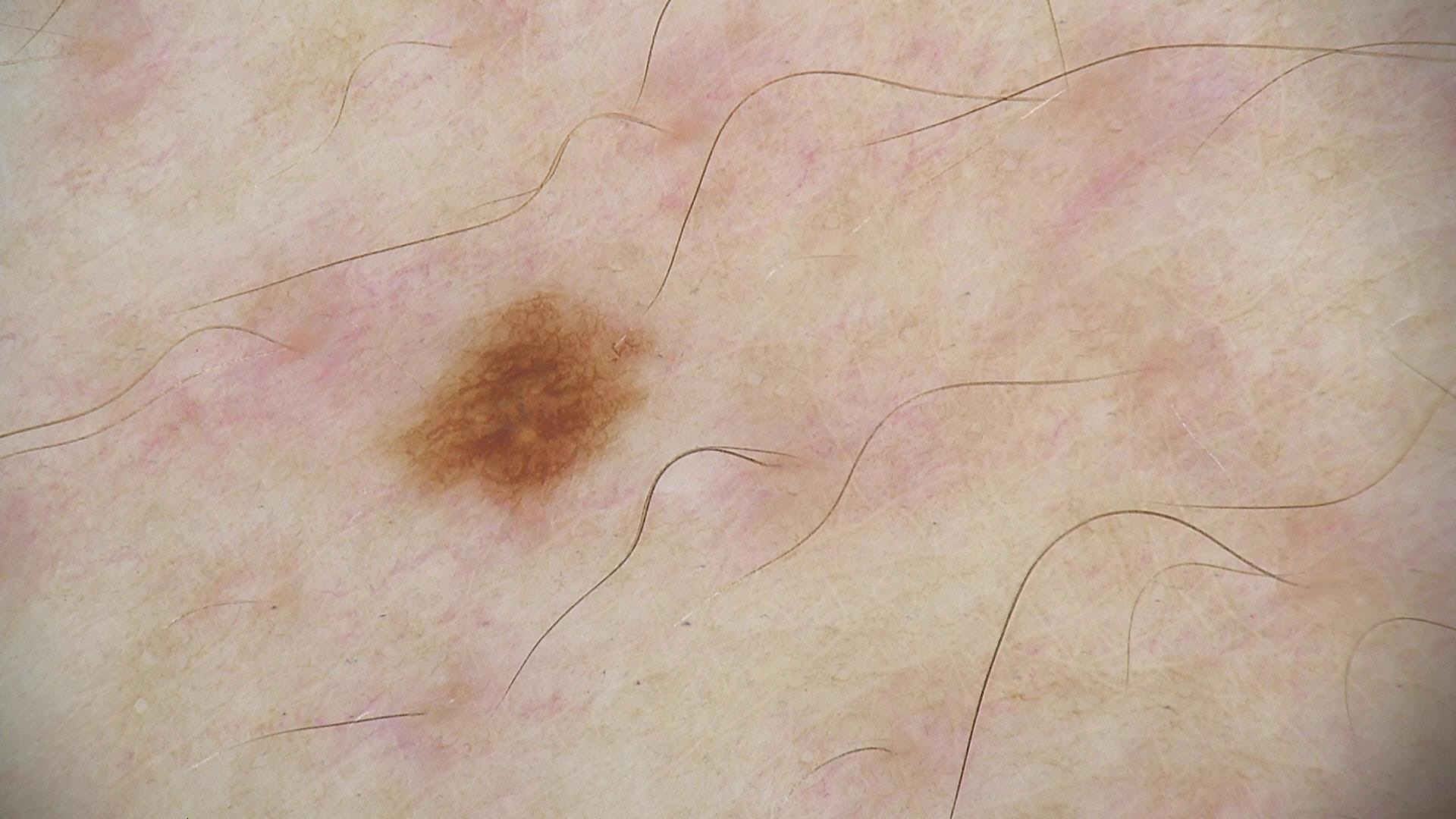Impression:
Consistent with a dysplastic junctional nevus.